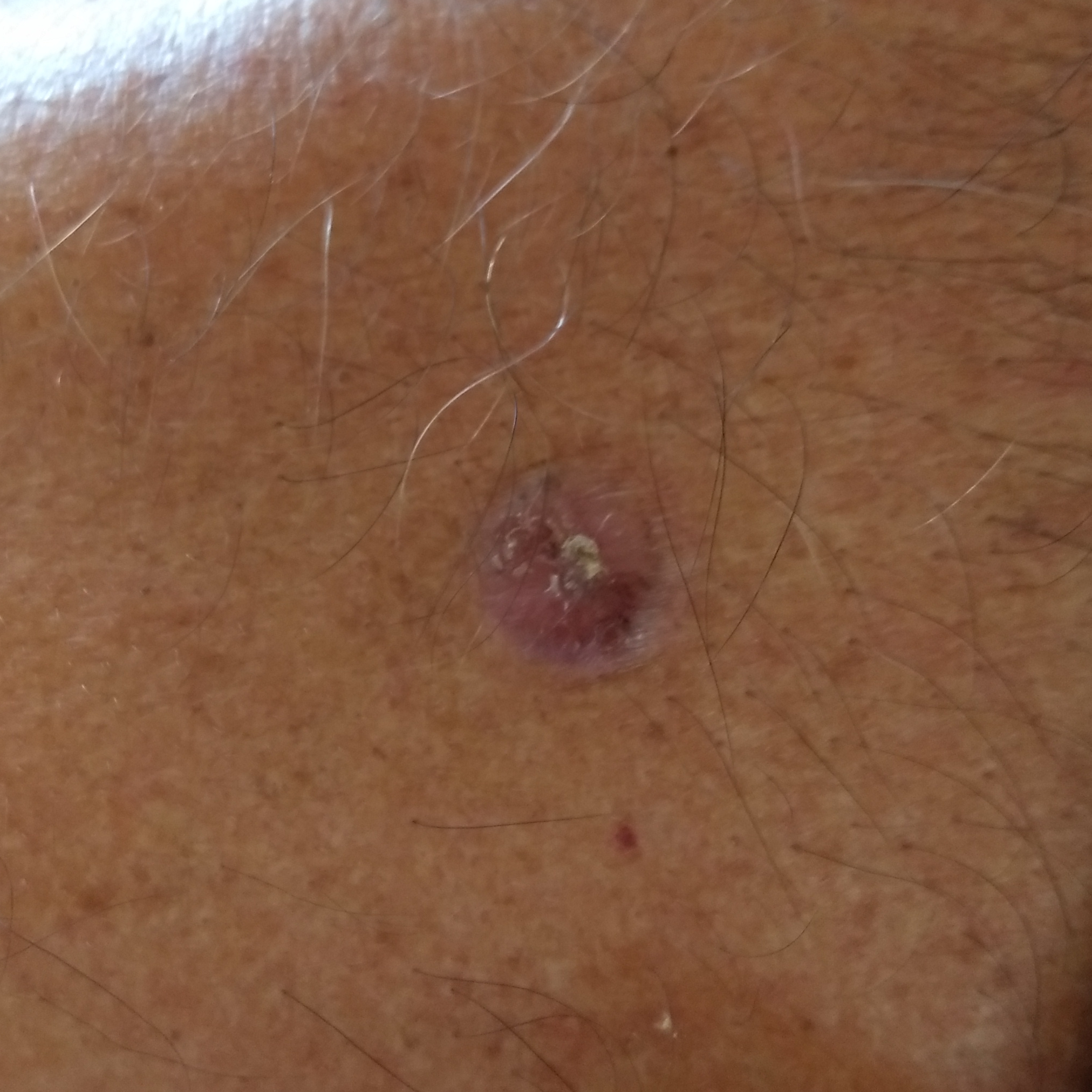exposure history = prior skin cancer (patient or family), pesticide exposure, no tobacco use
Fitzpatrick = III
body site = the back
size = 14 × 13 mm
symptoms = bleeding, itching, pain, elevation / no growth, no change in appearance
diagnosis = basal cell carcinoma (biopsy-proven)